A female patient aged 33 to 37 · recorded as Fitzpatrick II — 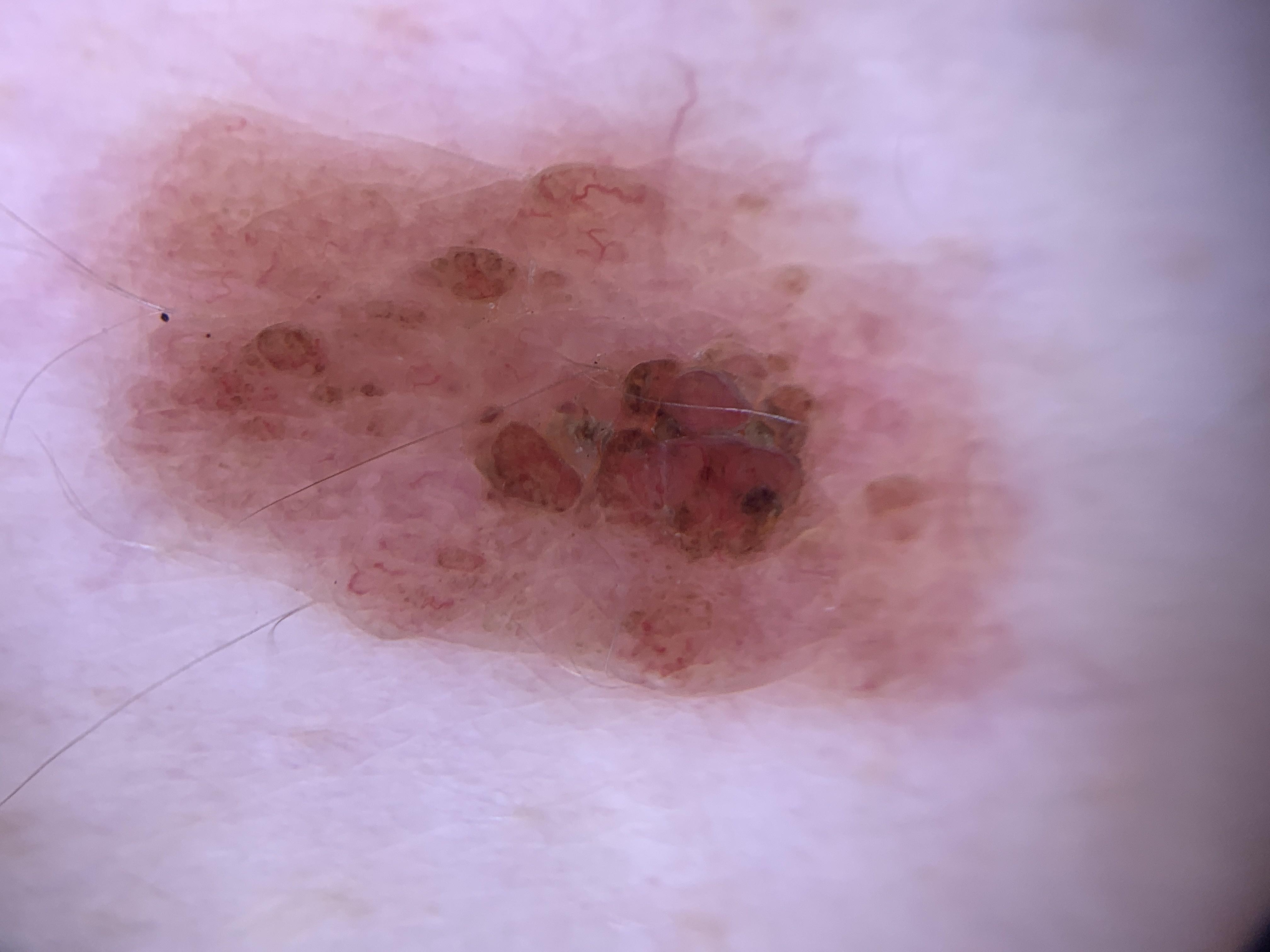Q: Where on the body is the lesion?
A: the trunk
Q: What did the workup show?
A: Nevus (biopsy-proven)